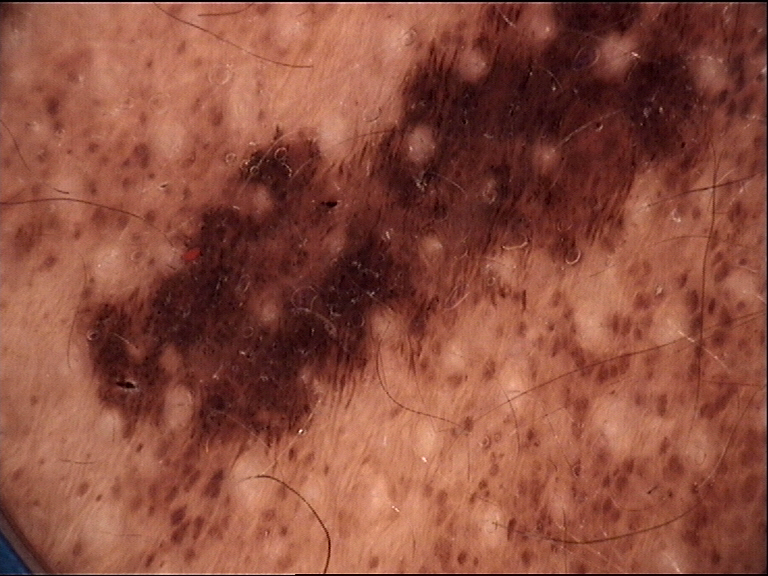image: dermoscopy
lesion_type:
  main_class: banal
  pattern: compound
diagnosis:
  name: congenital compound nevus
  code: ccb
  malignancy: benign
  super_class: melanocytic
  confirmation: expert consensus